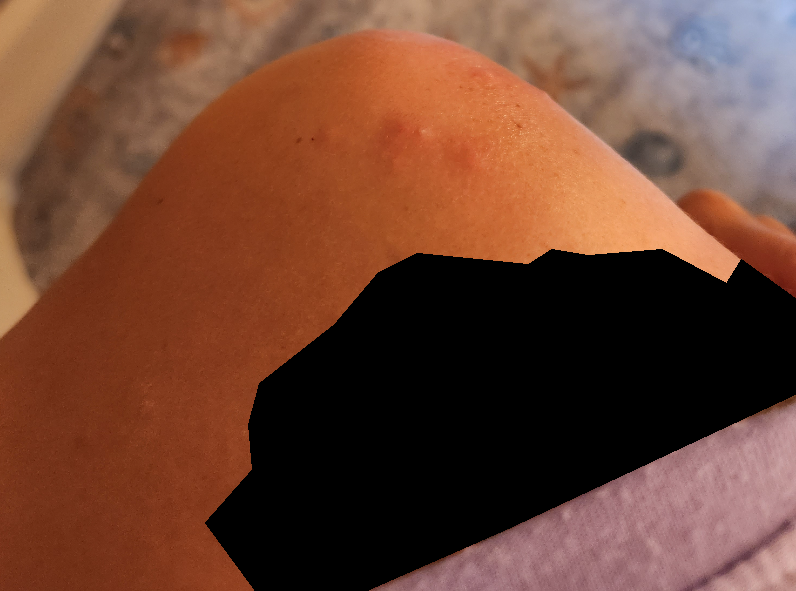Notes:
- assessment: indeterminate from the photograph
- patient-reported symptoms: burning
- associated systemic symptoms: none reported
- present for: about one day
- skin tone: Fitzpatrick phototype V; lay graders estimated Monk skin tone scale 3 or 5 (two reviewer pools disagreed)
- photo taken: at an angle
- described texture: raised or bumpy
- location: arm